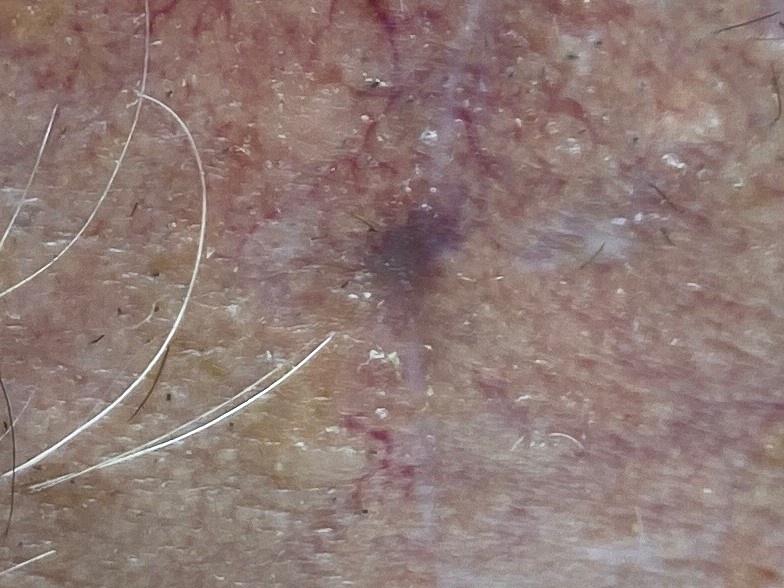Summary:
A male patient approximately 85 years of age or older. A wide-field clinical photograph of a skin lesion. The lesion involves the head or neck.
Conclusion:
The biopsy diagnosis was a squamous cell carcinoma.